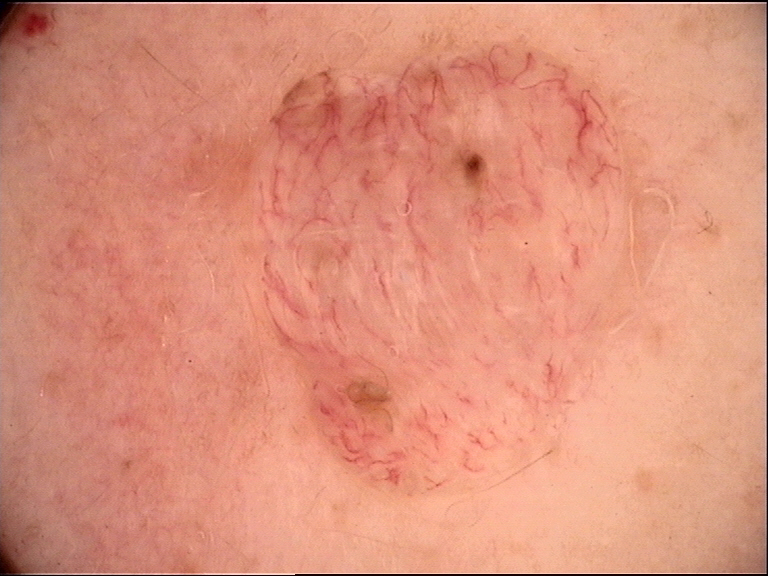Findings:
A dermoscopic image of a skin lesion.
Impression:
Classified as a banal lesion — a dermal nevus.